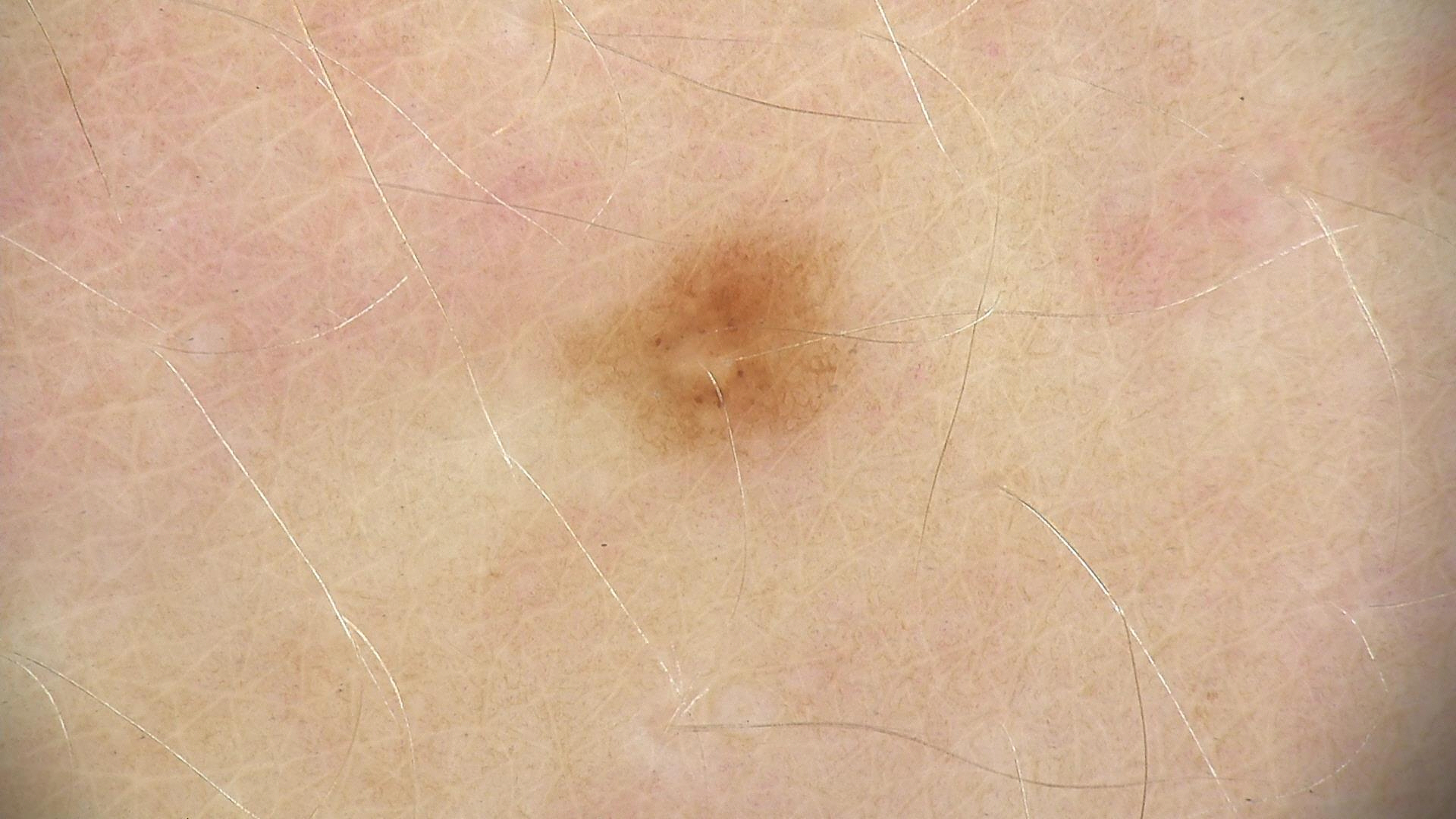diagnosis: dysplastic junctional nevus (expert consensus).